Skin tone: Fitzpatrick skin type III; present for less than one week; the photograph is a close-up of the affected area; self-categorized by the patient as skin that appeared healthy to them; the affected area is the arm; the subject is 18–29, male: 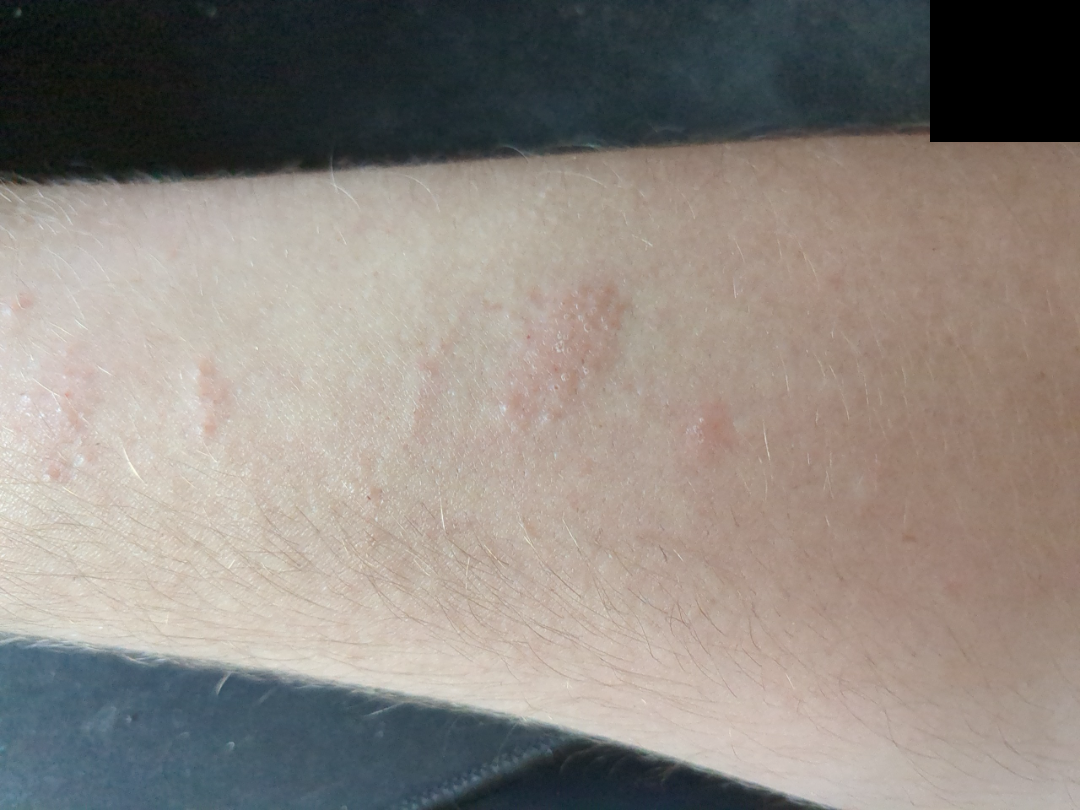In keeping with Allergic Contact Dermatitis.